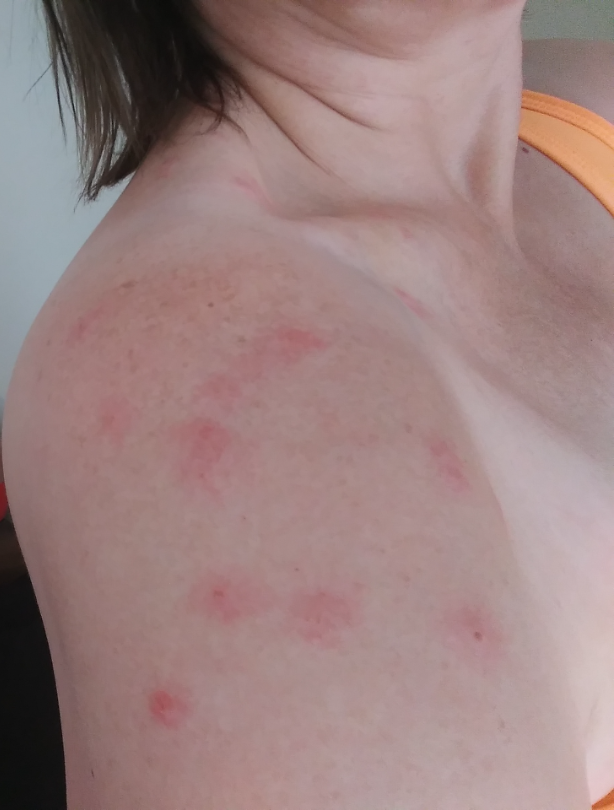The affected area is the arm and head or neck. Texture is reported as raised or bumpy. This is a close-up image. Reported lesion symptoms include itching. On remote review of the image: most consistent with Insect Bite.